A macroscopic clinical photograph of a skin lesion. A female patient aged 59. Referred with a clinical suspicion of melanocytic nevus.
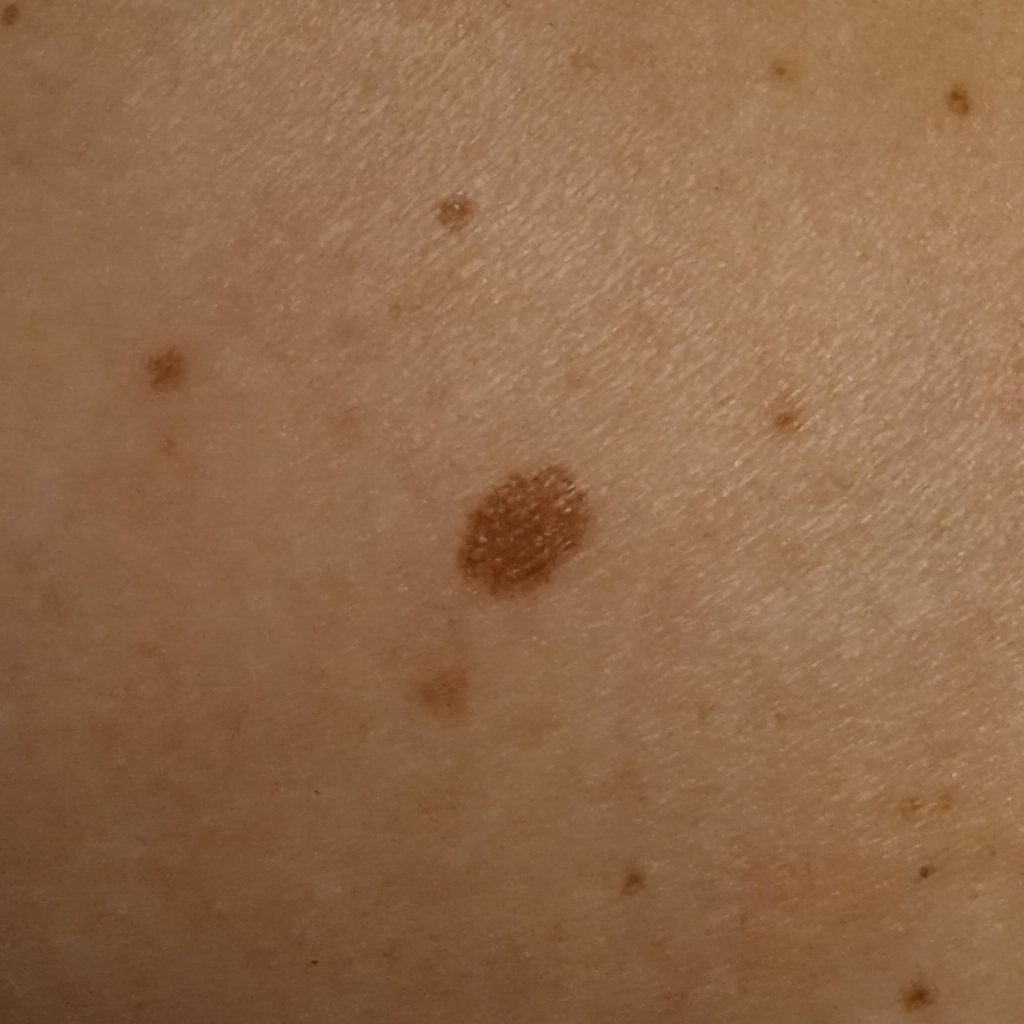Findings:
The lesion measures approximately 6.7 mm.
Conclusion:
The biopsy diagnosis was an atypical (dysplastic) nevus, following excision.